The affected area is the arm, head or neck and back of the hand. The contributor is a male aged 40–49. An image taken at an angle. The patient described the issue as a rash. Skin tone: FST III; lay reviewers estimated Monk Skin Tone 3 or 4 (two reviewer pools). Symptoms reported: enlargement and itching. Present for one to four weeks. The patient indicates the lesion is raised or bumpy — 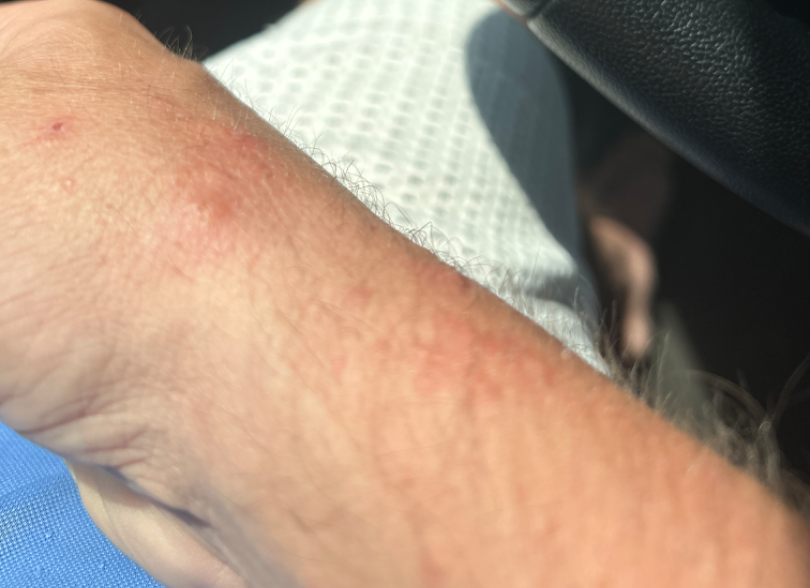differential: Deep fungal infection